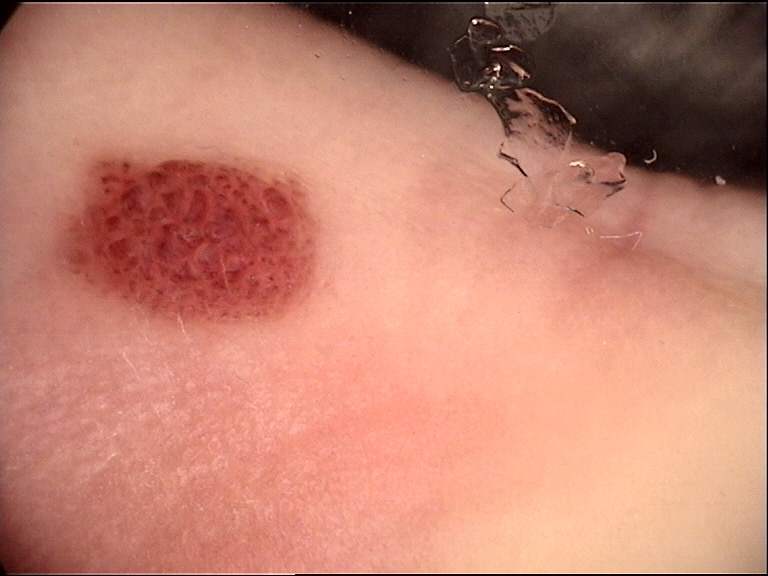image type: dermoscopy, category: banal, class: acral compound nevus (expert consensus).